A close-up photograph:
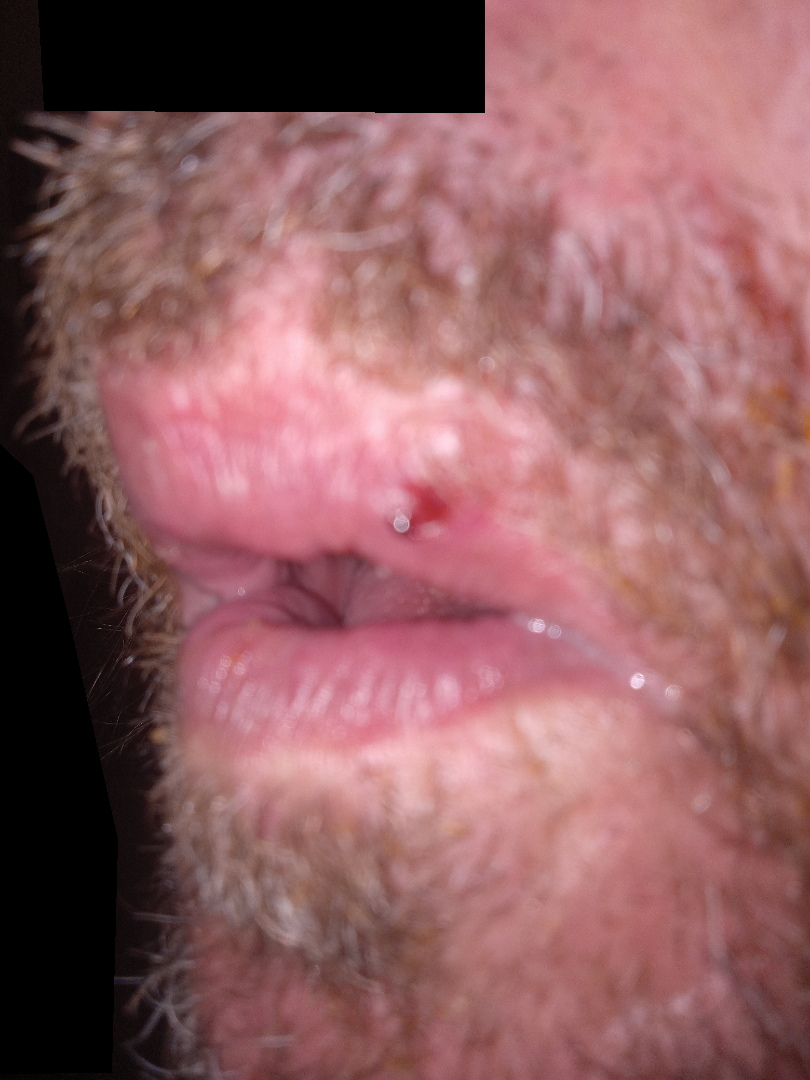Review:
The reviewer was unable to grade this case for skin condition.